The subject is a female aged 43-47 · a dermoscopic view of a skin lesion.
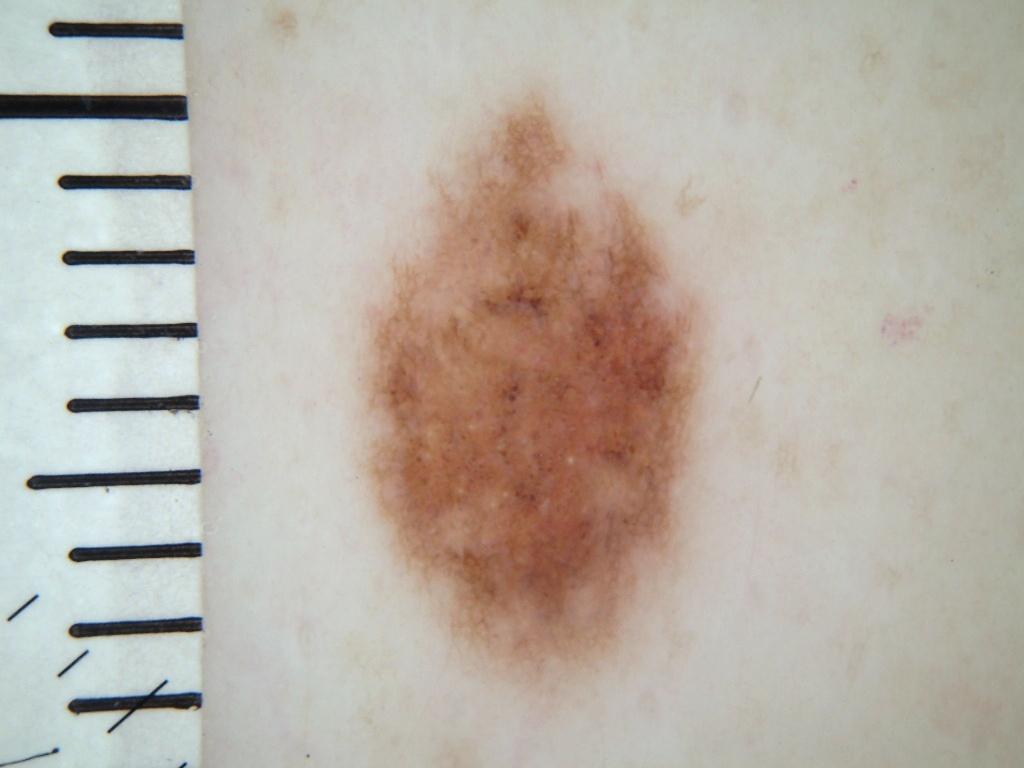<record>
  <lesion_location>
    <bbox_xyxy>362, 92, 707, 699</bbox_xyxy>
  </lesion_location>
  <lesion_extent>moderate</lesion_extent>
  <dermoscopic_features>
    <present>pigment network, globules, milia-like cysts</present>
    <absent>negative network, streaks</absent>
  </dermoscopic_features>
  <diagnosis>
    <name>melanocytic nevus</name>
    <malignancy>benign</malignancy>
    <lineage>melanocytic</lineage>
    <provenance>clinical</provenance>
  </diagnosis>
</record>